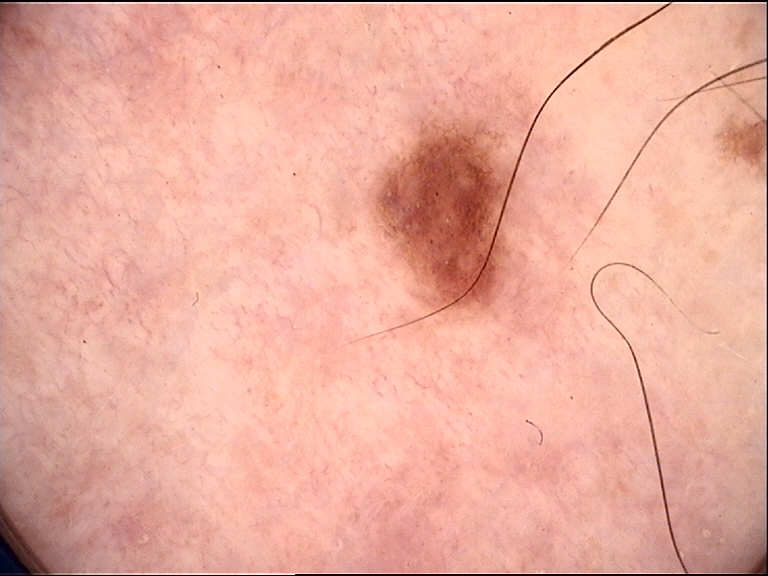A dermoscopic close-up of a skin lesion. Consistent with a benign lesion — a dysplastic junctional nevus.